Texture is reported as raised or bumpy, self-categorized by the patient as a rash, the patient reports itching, the contributor is a female aged 50–59, the patient also reports shortness of breath, located on the leg, the patient reports the condition has been present for less than one week, close-up view:
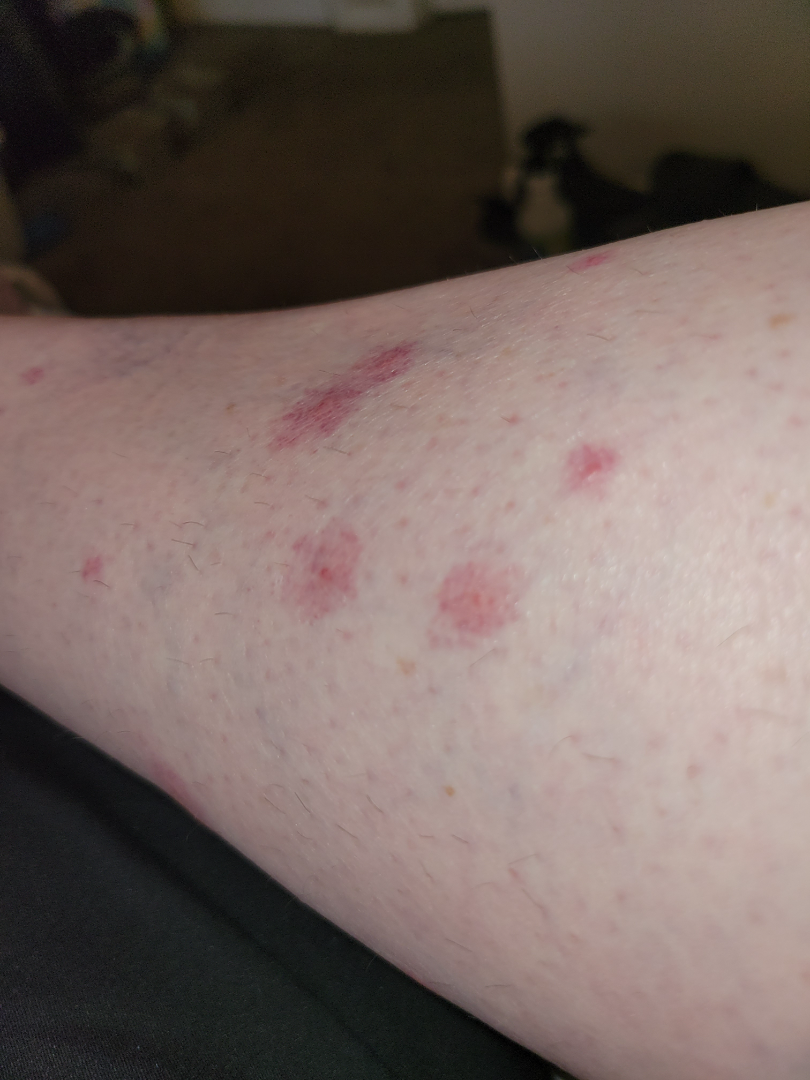{
  "differential": "Insect Bite"
}